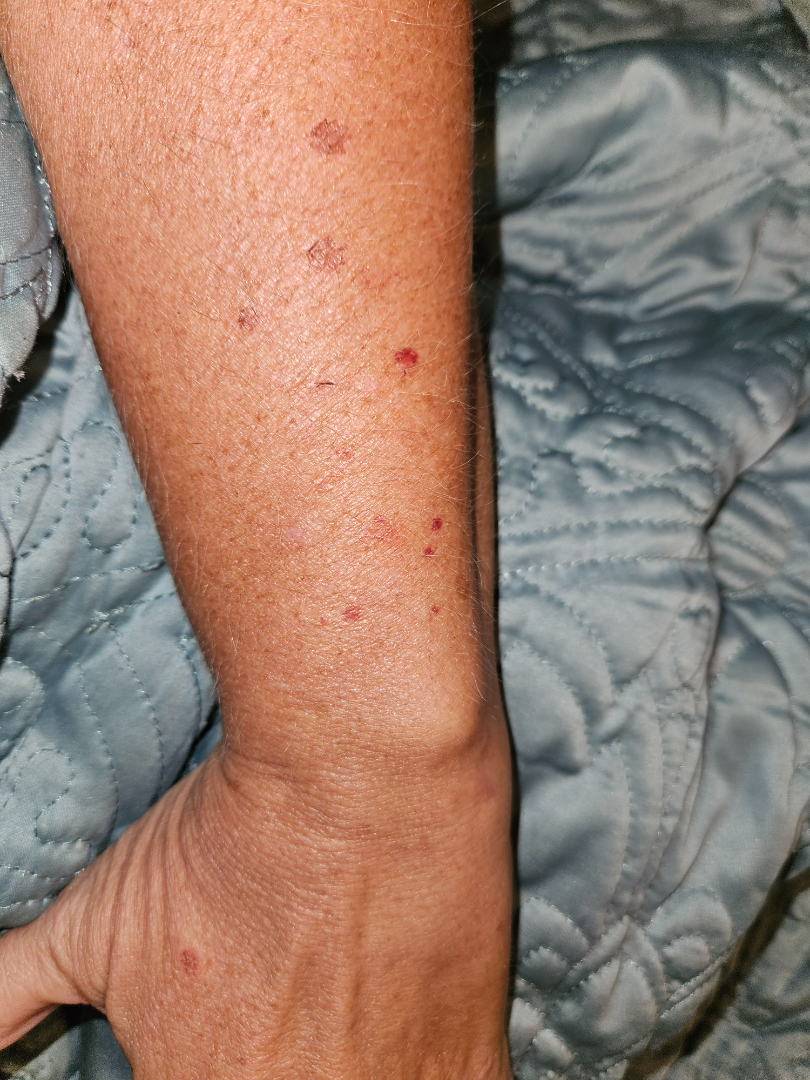| feature | finding |
|---|---|
| assessment | Burn of forearm; Abrasion, scrape, or scab; and Actinic Keratosis were considered with similar weight |